The patient reported no systemic symptoms · texture is reported as flat · the photograph is a close-up of the affected area · the arm is involved · the patient considered this a rash · reported duration is one to four weeks · male patient, age 40–49 · the lesion is associated with enlargement and itching — 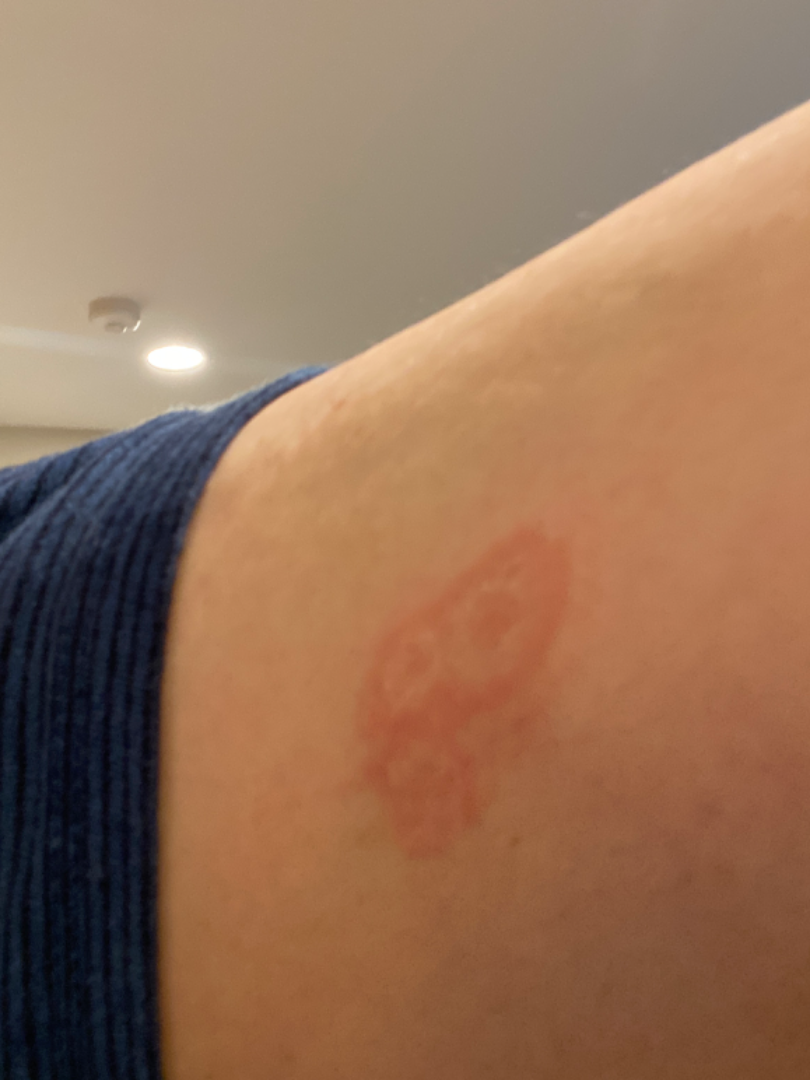{"differential": {"leading": ["Erythema multiforme"]}}